A male patient aged approximately 75. A skin lesion imaged with contact-polarized dermoscopy. Recorded as Fitzpatrick phototype II — 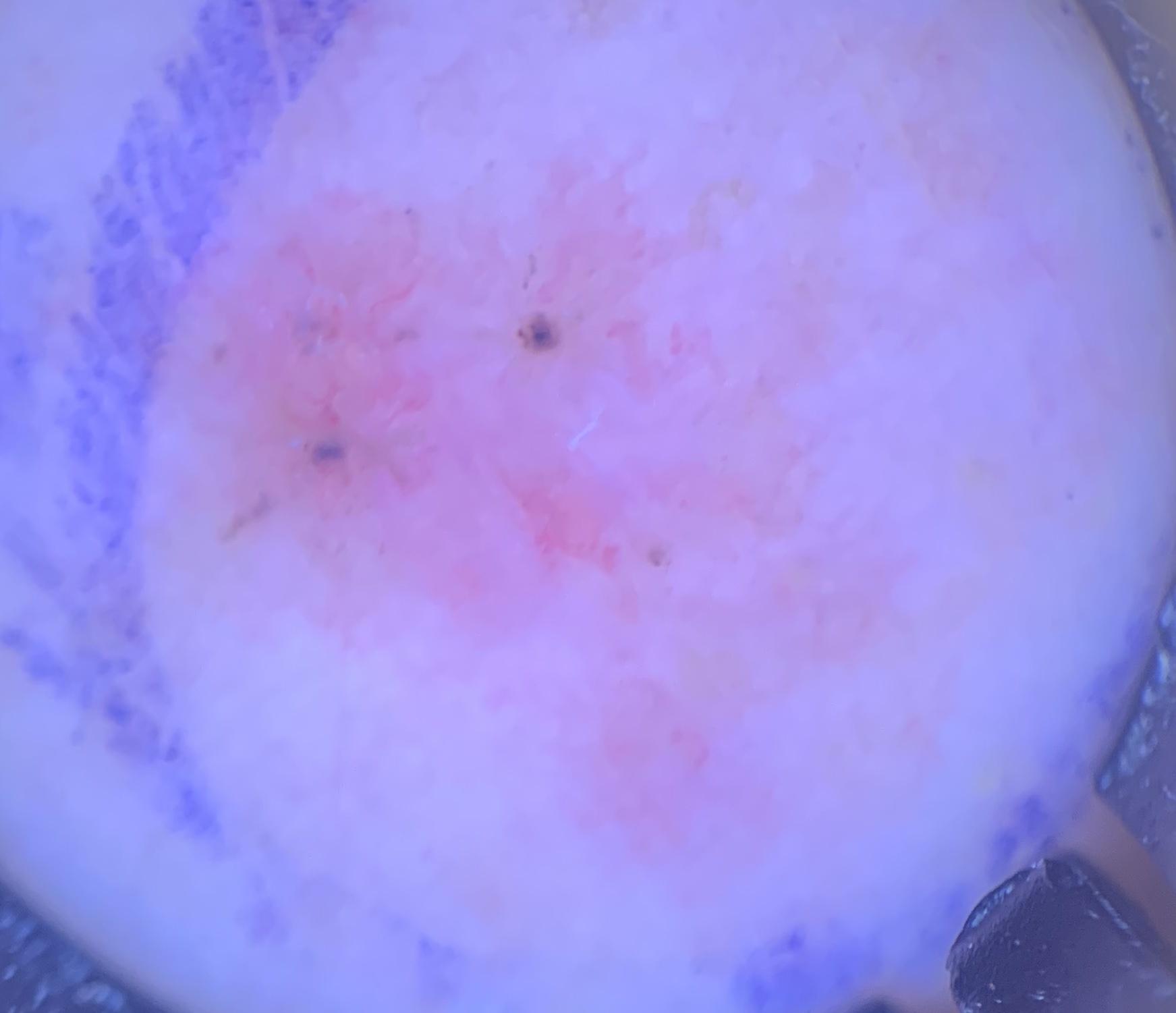Clinical context: Located on the posterior trunk. Conclusion: Histopathologically confirmed as a malignant, adnexal lesion — a basal cell carcinoma.